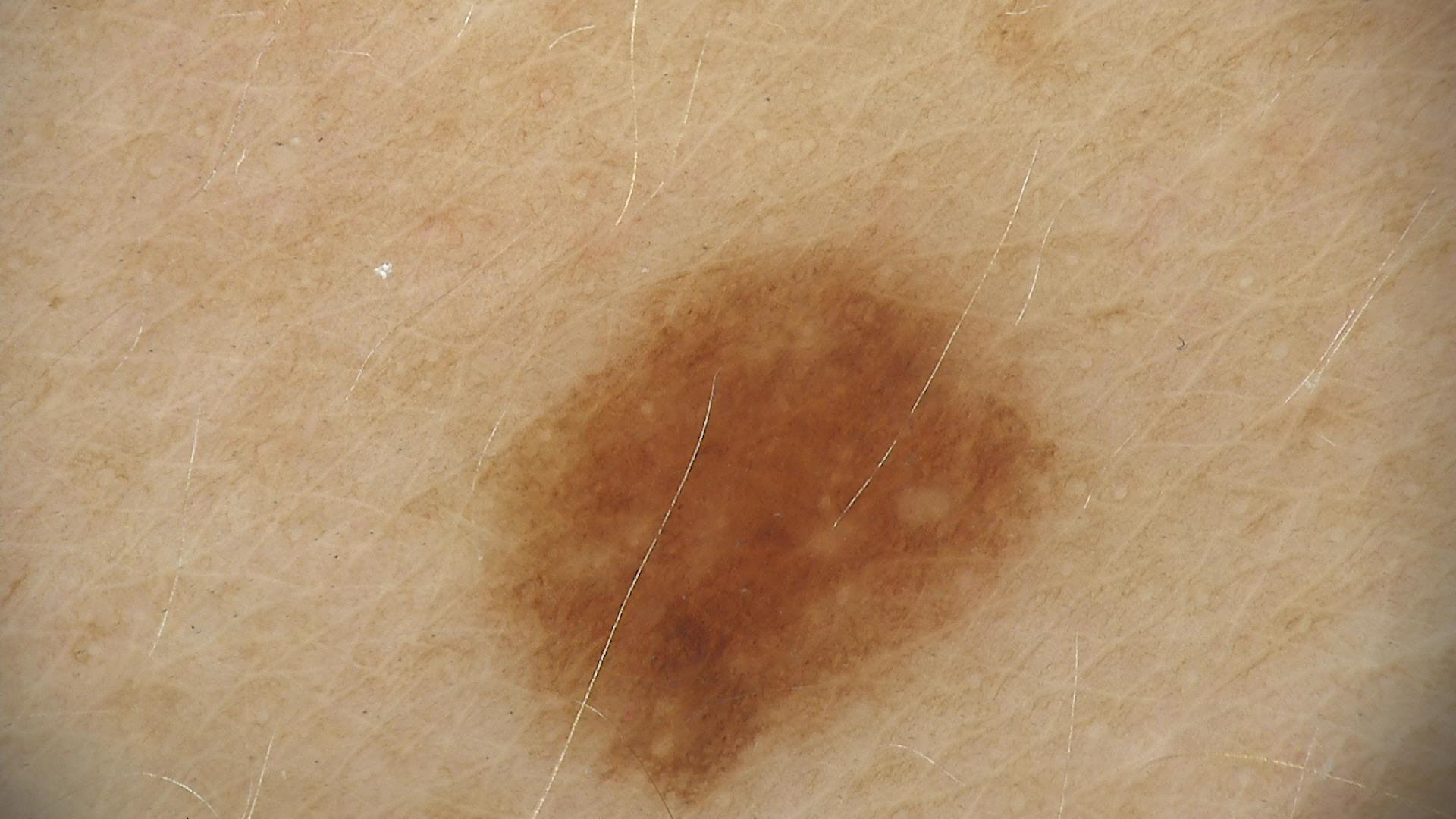Conclusion: Consistent with a dysplastic junctional nevus.